This is a close-up image. The patient is a female aged 50–59. The lesion involves the leg — 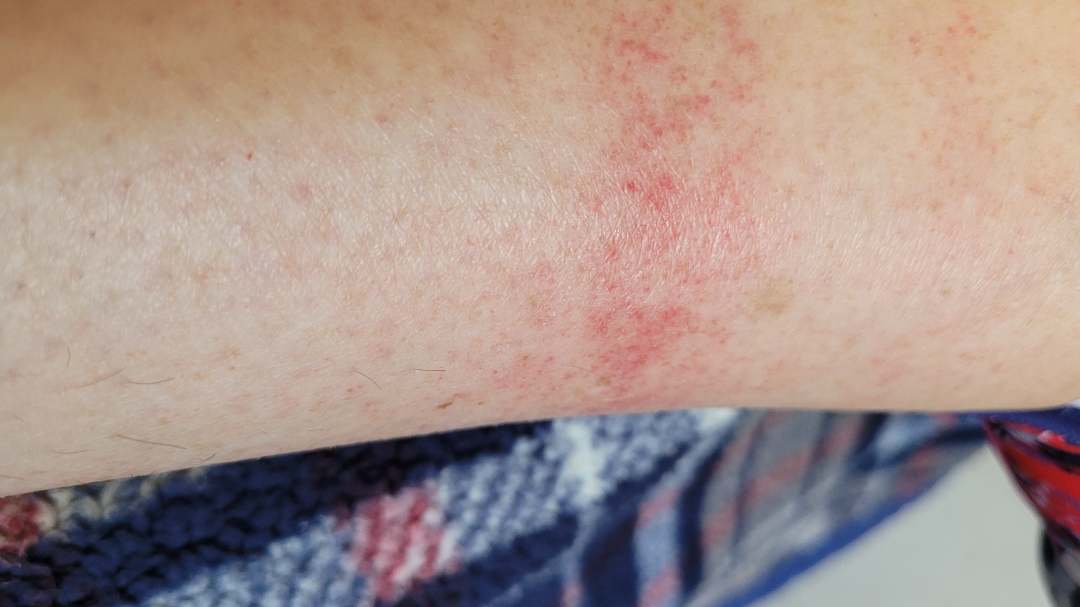Q: What conditions are considered?
A: Acute dermatitis, NOS (possible); Allergic Contact Dermatitis (possible); Irritant Contact Dermatitis (possible)